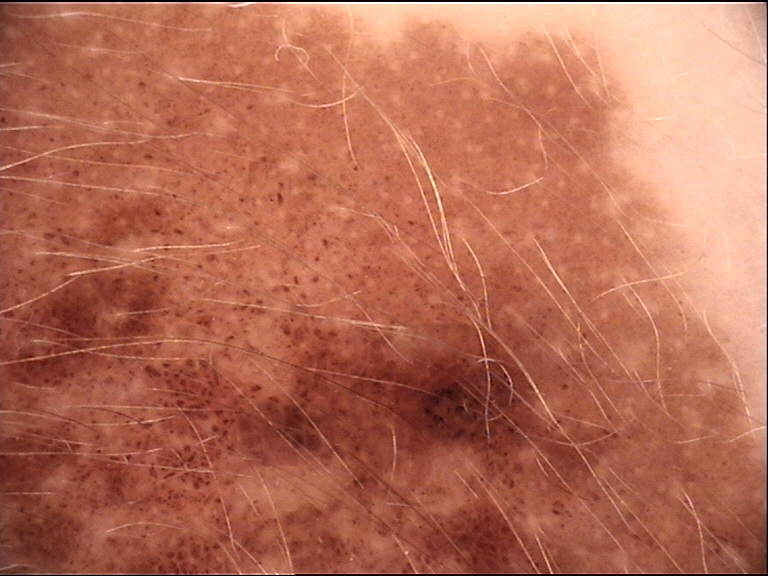Conclusion:
Diagnosed as a banal lesion — a congenital junctional nevus.